A dermatoscopic image of a skin lesion · a male subject aged 83 or older: 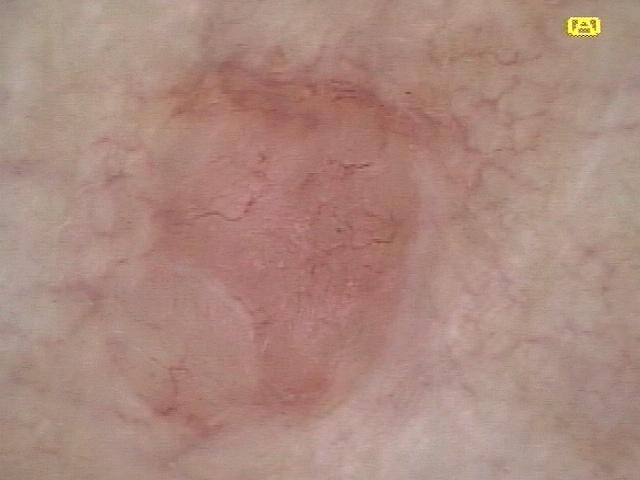The lesion involves the posterior trunk. Histopathological examination showed a basal cell carcinoma.